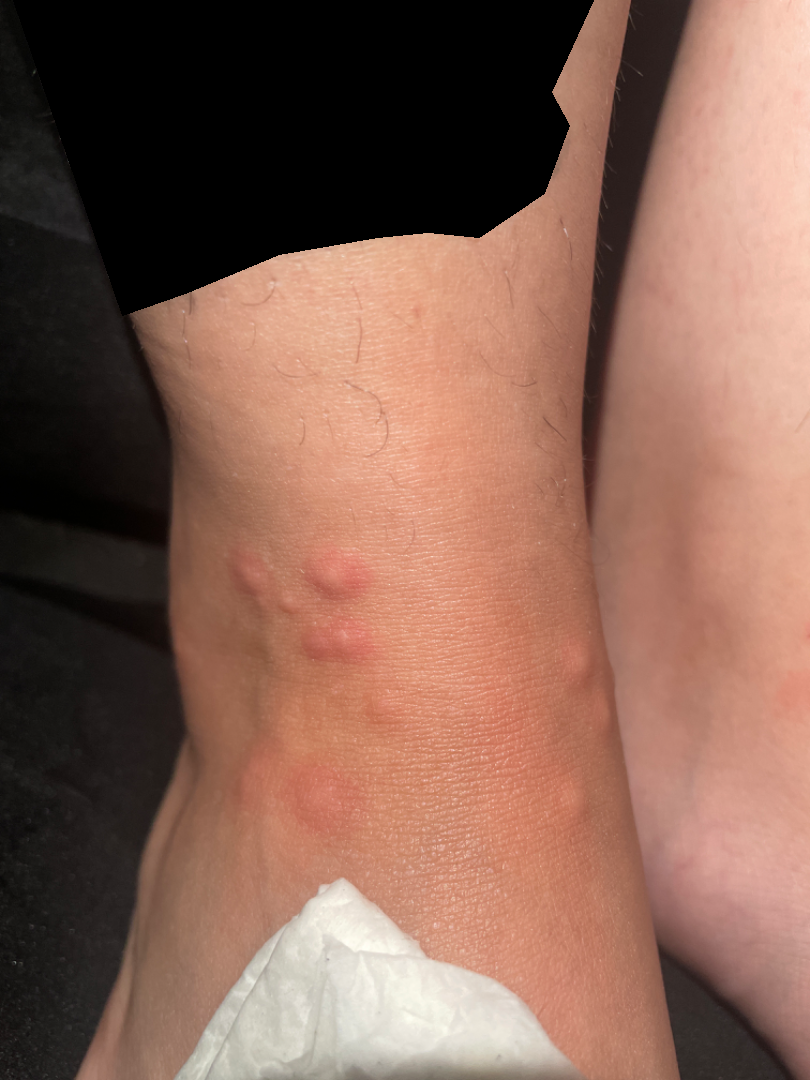photo taken=close-up | anatomic site=top or side of the foot | patient's own categorization=a rash | surface texture=fluid-filled and raised or bumpy | assessment=one reviewing dermatologist: consistent with Insect Bite.